A skin lesion imaged with a dermatoscope.
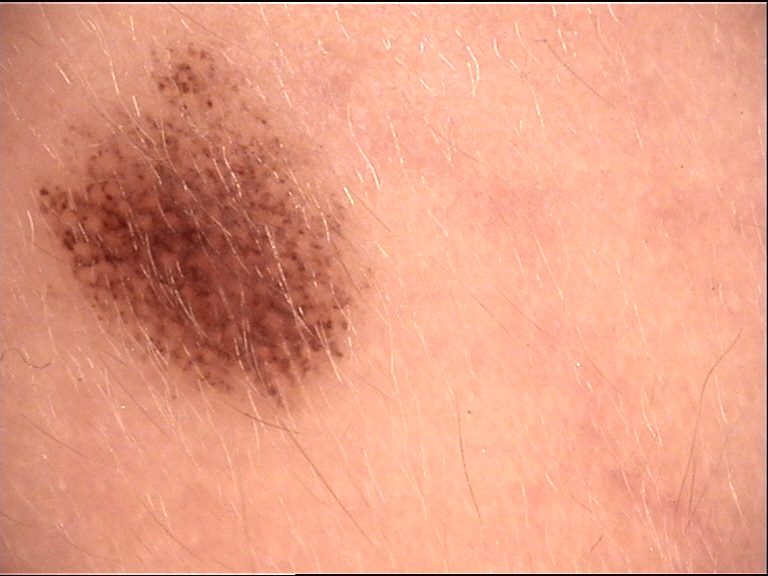Classified as a dysplastic junctional nevus.